Located on the head or neck; an image taken at an angle: 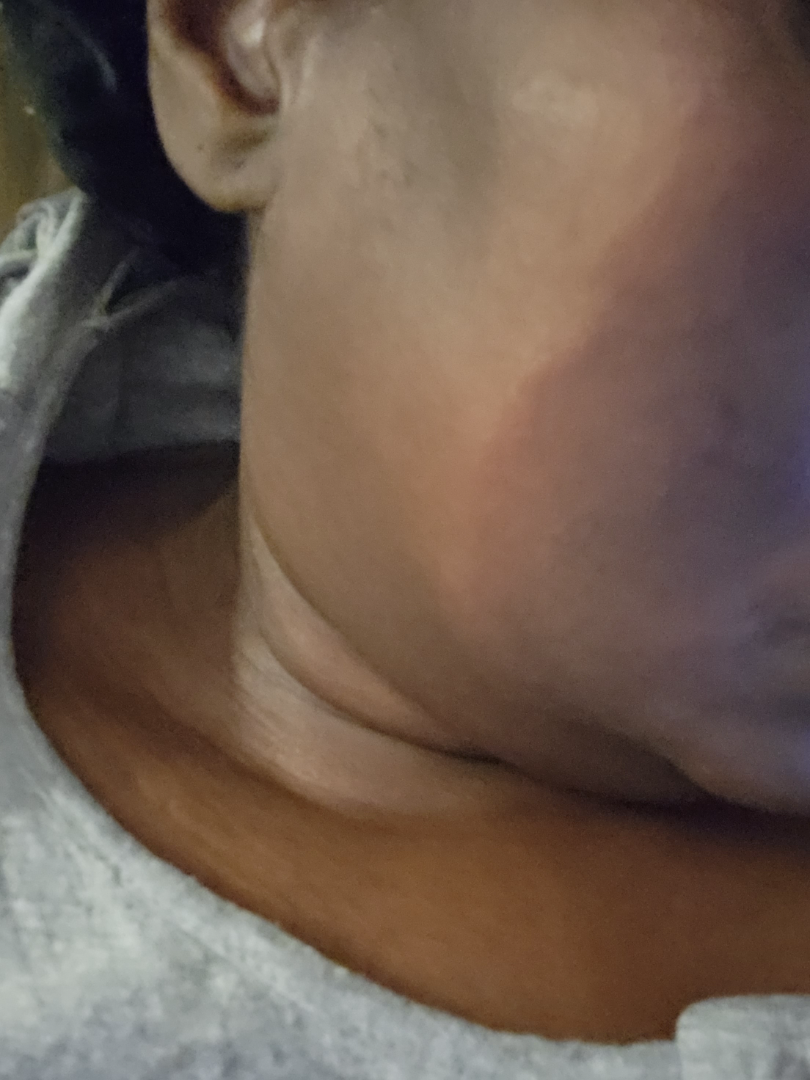Findings:
On remote dermatologist review: the leading impression is Post-Inflammatory hyperpigmentation.